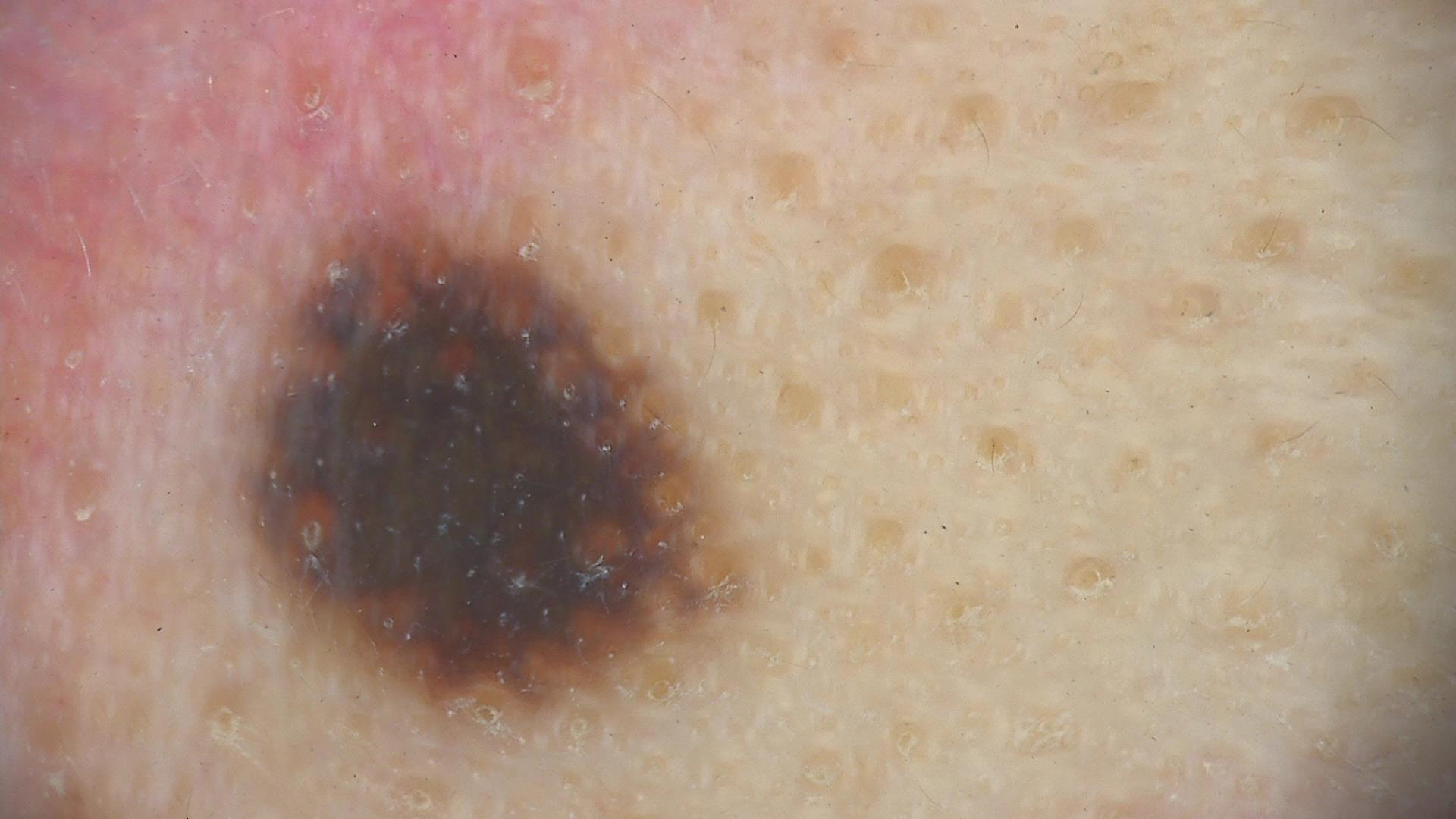| key | value |
|---|---|
| modality | dermoscopy |
| classification | banal |
| class | congenital compound nevus (expert consensus) |